Dermoscopy of a skin lesion.
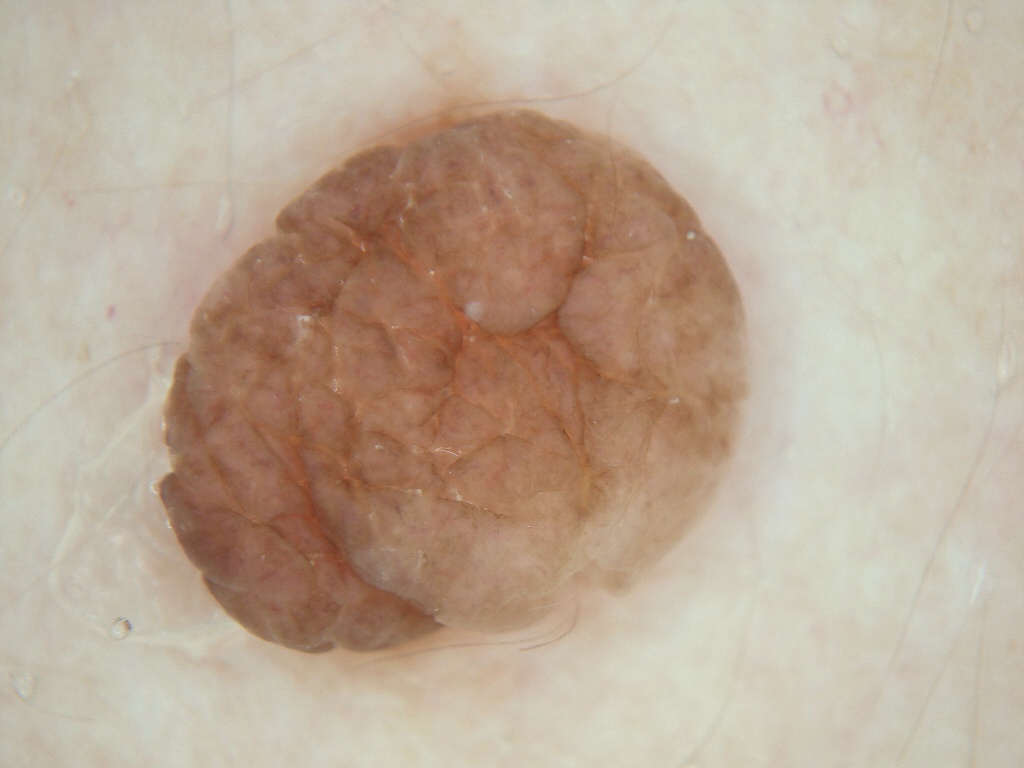A large lesion occupying much of the field.
The lesion is located at 156 92 742 664.
Dermoscopic review identifies no streaks, negative network, globules, milia-like cysts, or pigment network.
Diagnosed as a melanocytic nevus.